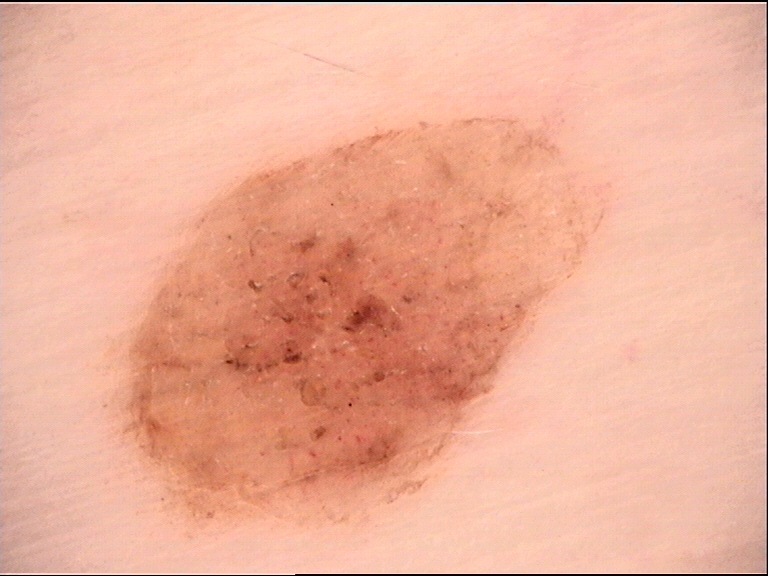Labeled as a dermal nevus.